A male patient aged 58 to 62: 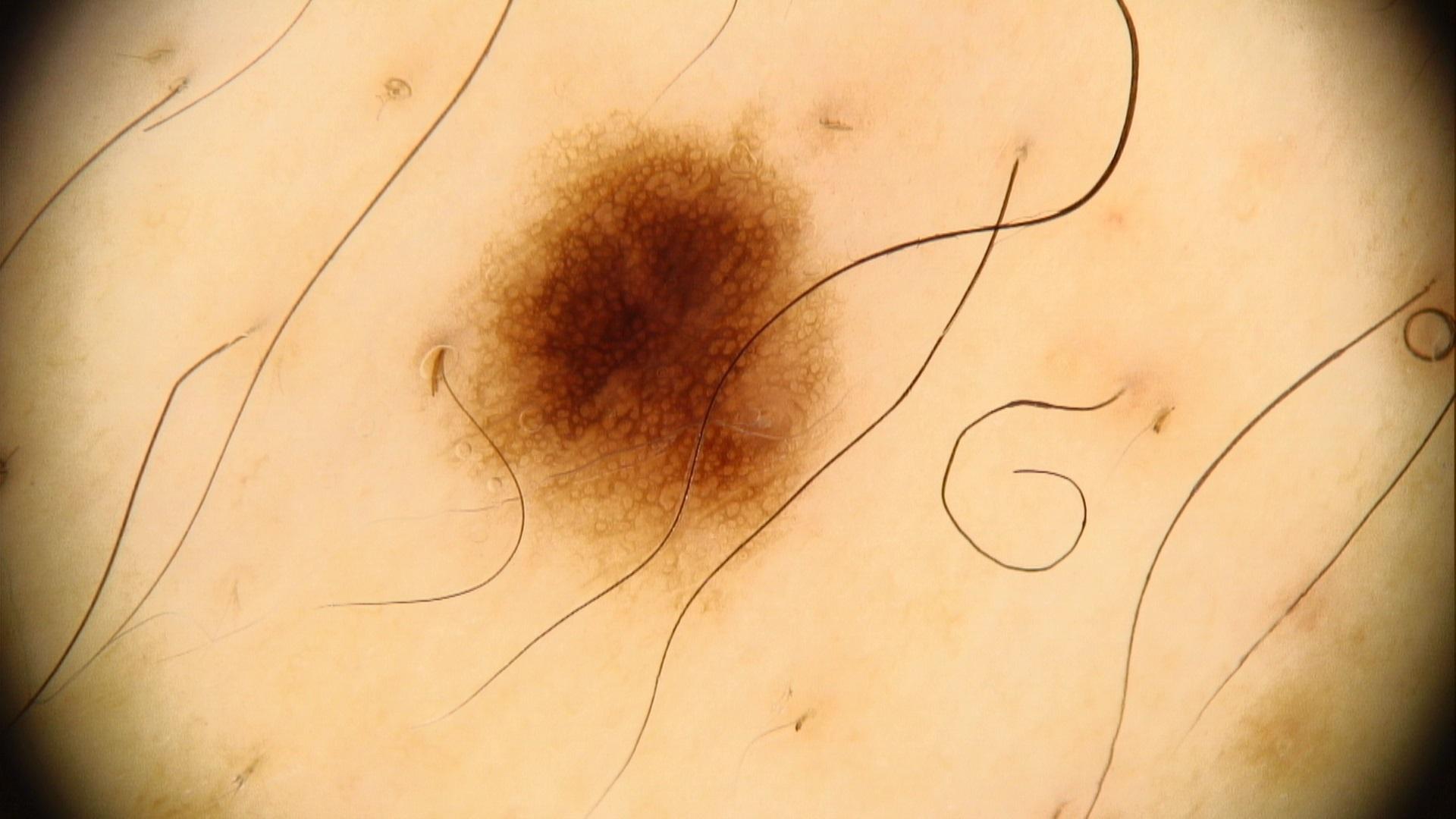The lesion is located on a lower extremity. The diagnostic impression was a melanocytic lesion — a nevus.